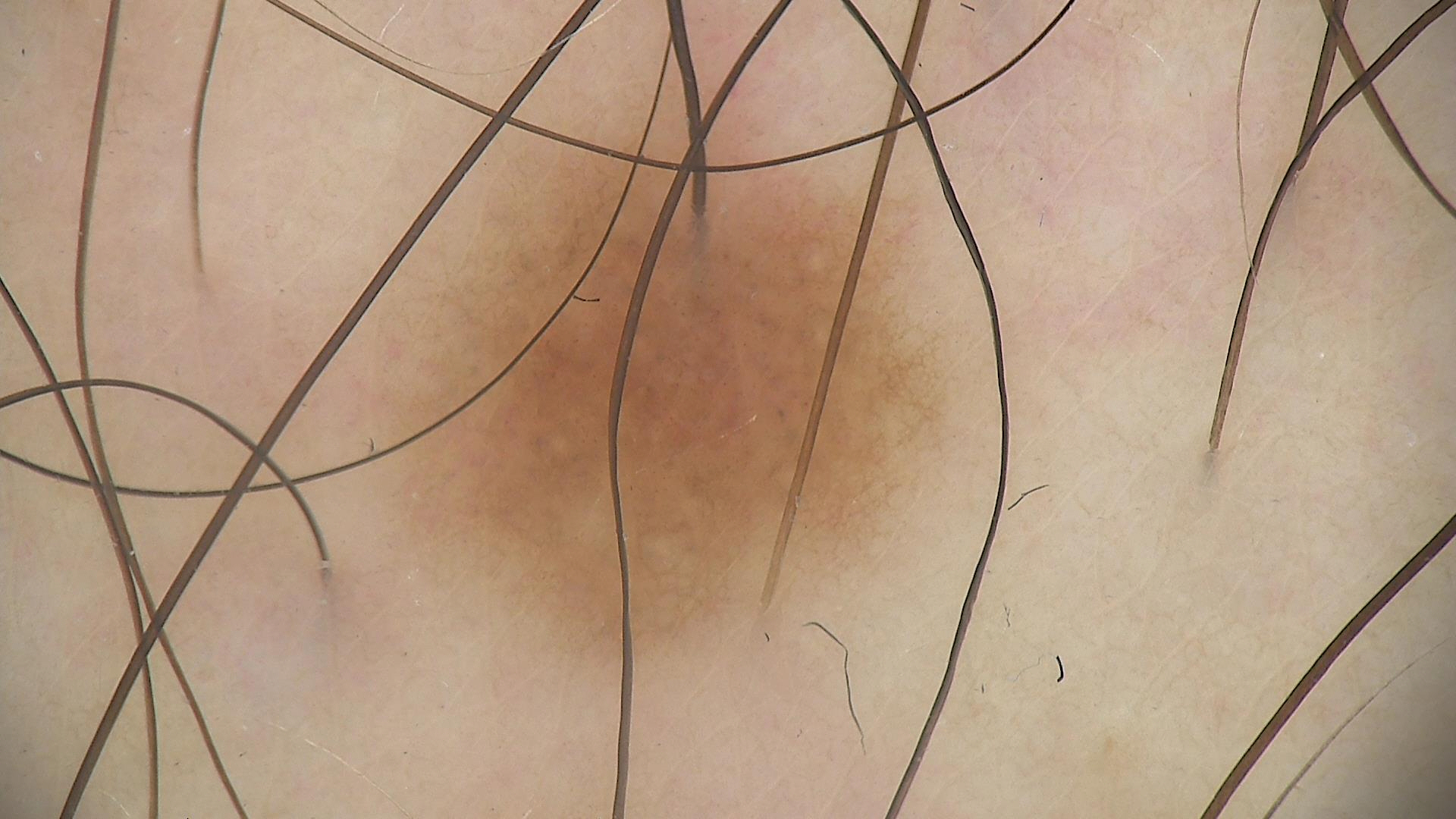Classified as a junctional nevus.